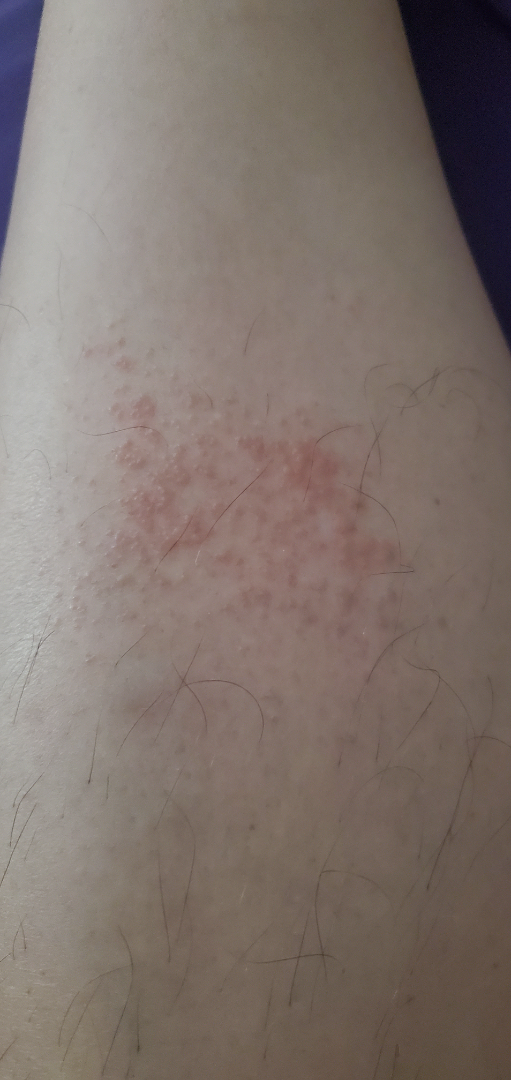On remote review of the image: Contact dermatitis (most likely); Eczema (unlikely); Allergic Contact Dermatitis (unlikely); Miliaria (unlikely); Acute dermatitis, NOS (unlikely).